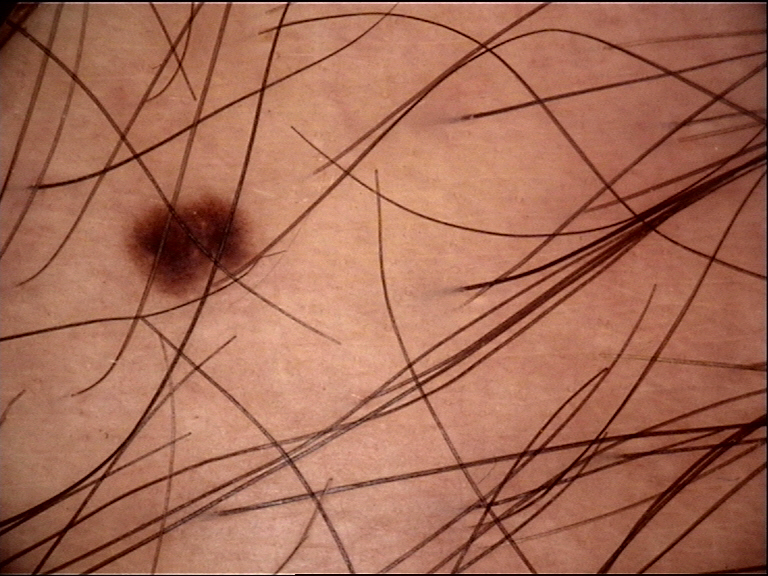diagnostic label = dysplastic junctional nevus (expert consensus).